A clinical close-up photograph of a skin lesion. A patient aged 80: 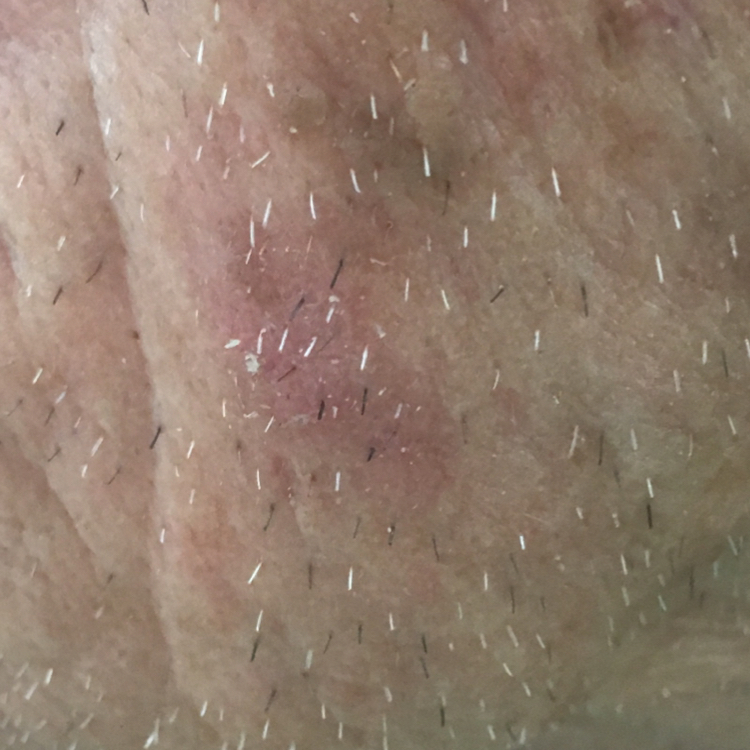anatomic site=the face | patient-reported symptoms=none reported | diagnostic label=actinic keratosis (clinical consensus).